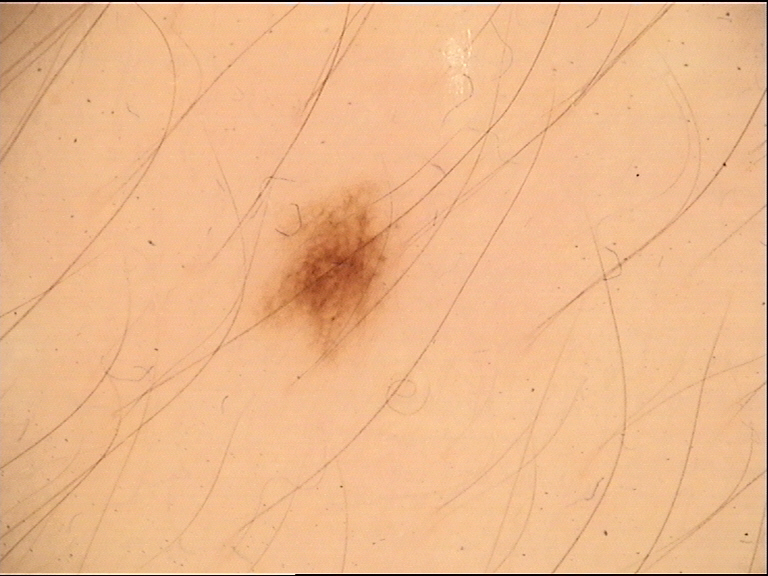Case: A dermoscopic close-up of a skin lesion. This is a banal lesion. Conclusion: Consistent with a junctional nevus.